A close-up photograph: 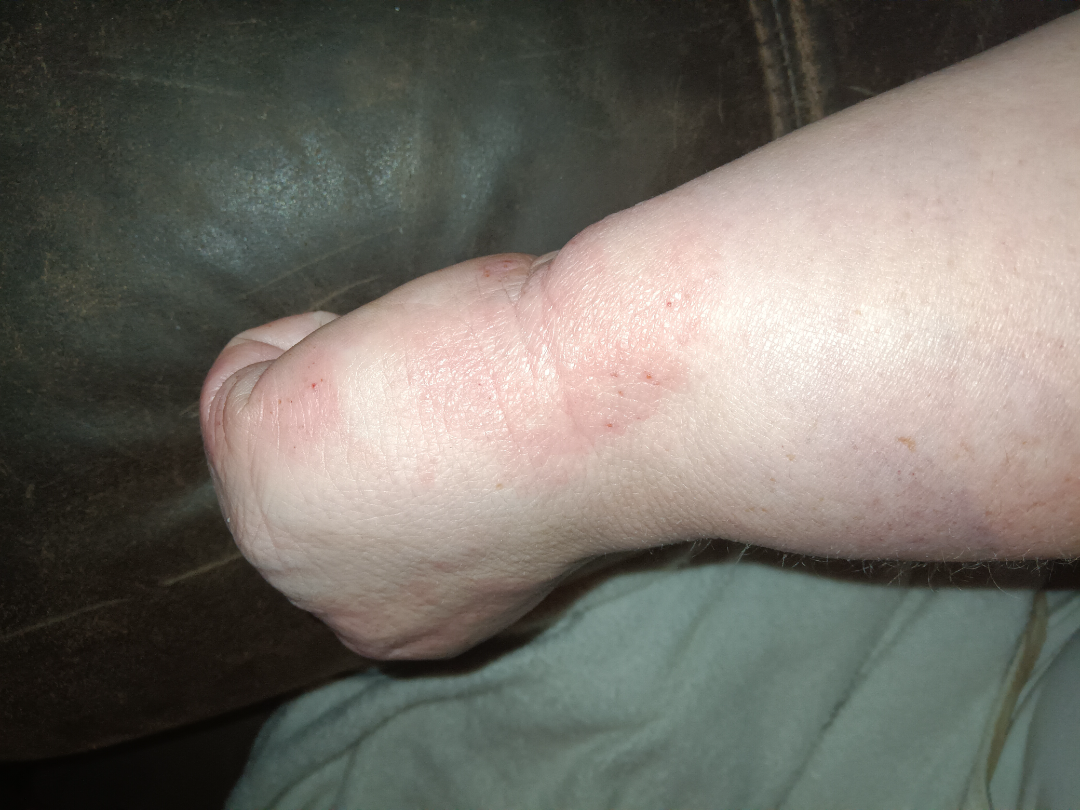<dermatology_case>
<differential>
  <Eczema>0.67</Eczema>
  <Allergic Contact Dermatitis>0.33</Allergic Contact Dermatitis>
</differential>
</dermatology_case>